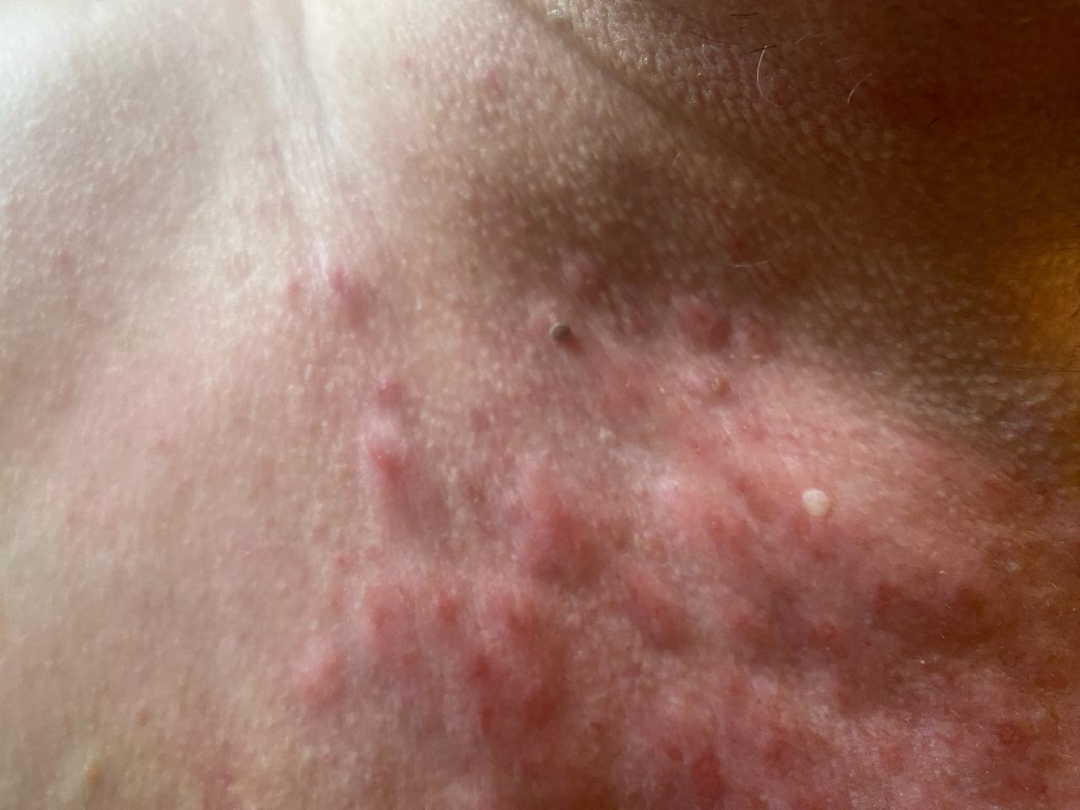No differential diagnosis could be assigned on photographic review. Located on the front of the torso and head or neck. This is a close-up image.